A female patient age 92. On a questionnaire the patient reported a family history of skin cancer and a personal history of cancer. The patient says their skin tans without first burning: 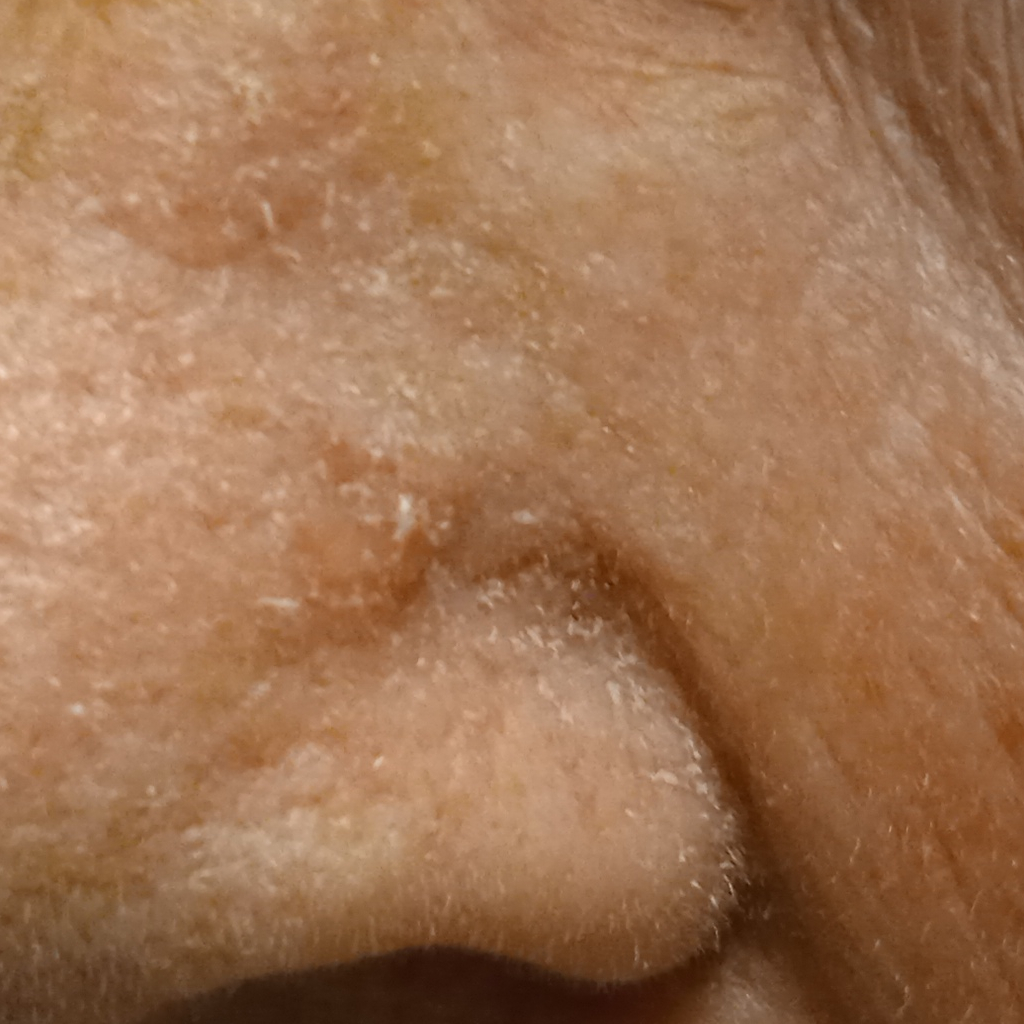The lesion involves the face.
Measuring roughly 7 mm.
The lesion was assessed as a basal cell carcinoma.